Located on the arm. The patient is 18–29, female. The photograph was taken at an angle — 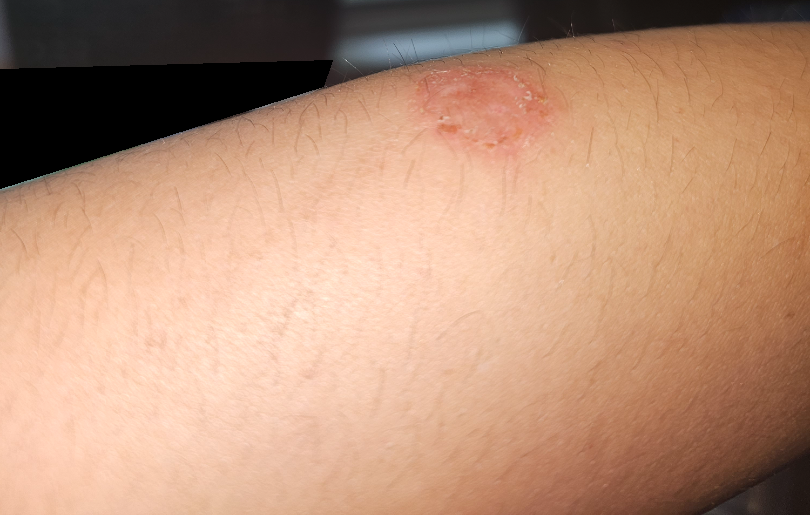Assessment: On independent review by the dermatologists, most likely Eczema; a more distant consideration is Psoriasis; less probable is Tinea; less likely is Deep fungal infection; a remote consideration is Cutaneous sarcoidosis; lower on the differential is Skin and soft tissue atypical mycobacterial infection.